A dermoscopic image of a skin lesion; a male patient, in their 40s.
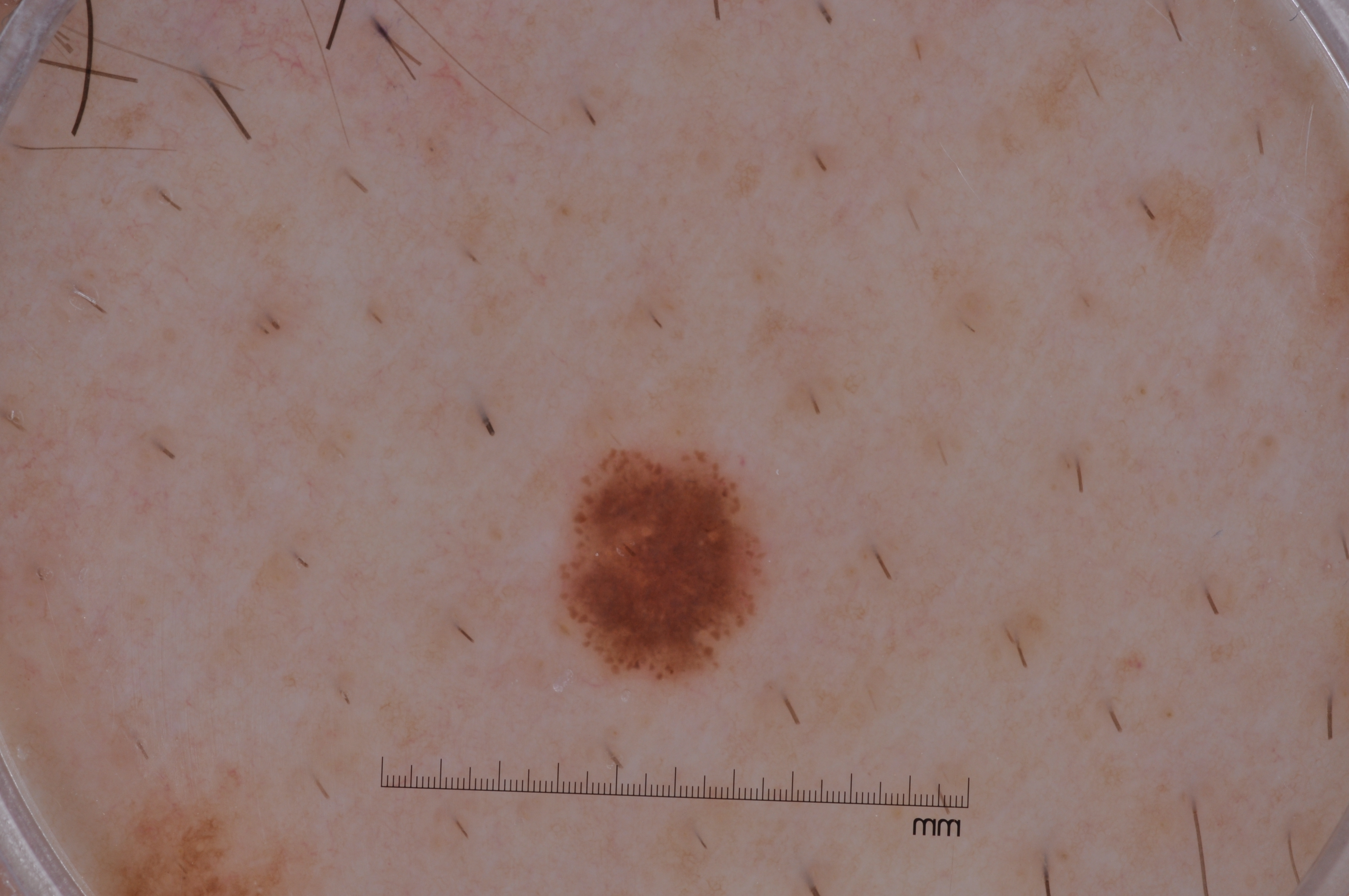Findings: Dermoscopic examination shows milia-like cysts; no pigment network, streaks, or negative network. The lesion takes up about 3% of the image. In (x1, y1, x2, y2) order, the visible lesion spans (569, 449, 759, 679). Impression: Consistent with a melanocytic nevus, a benign lesion.